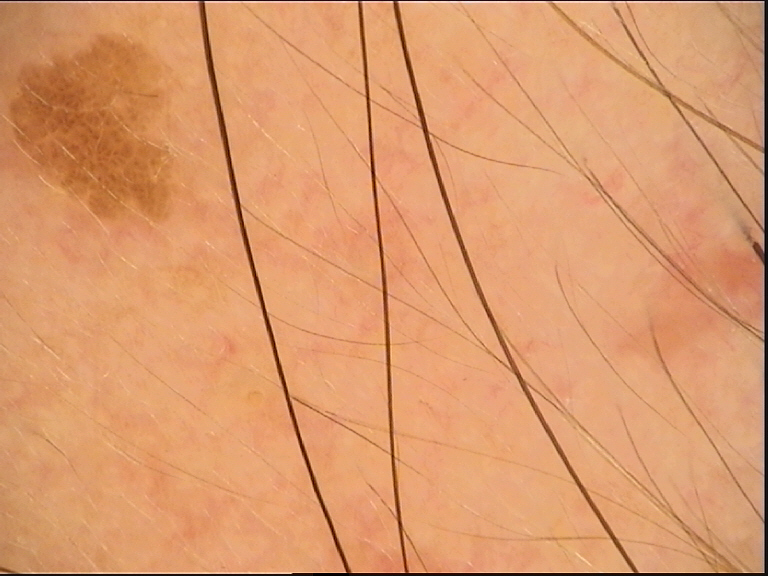class: seborrheic keratosis (expert consensus).